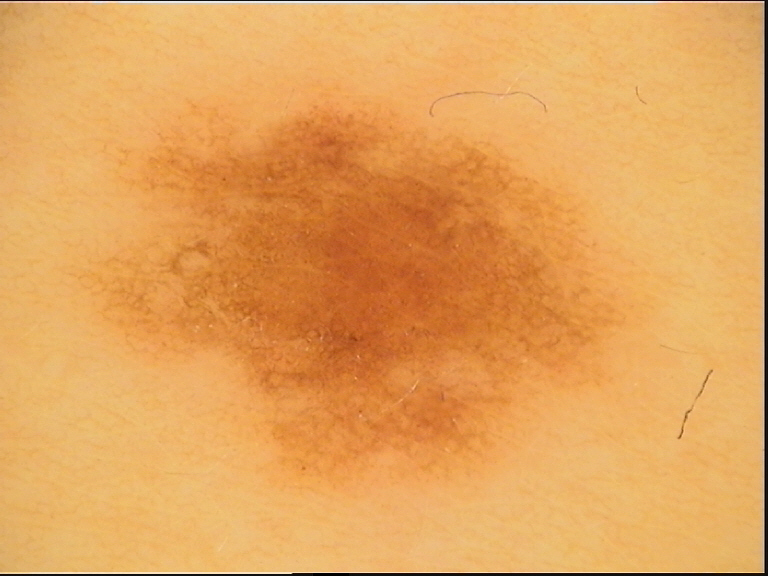image = dermoscopy, class = dysplastic junctional nevus (expert consensus).